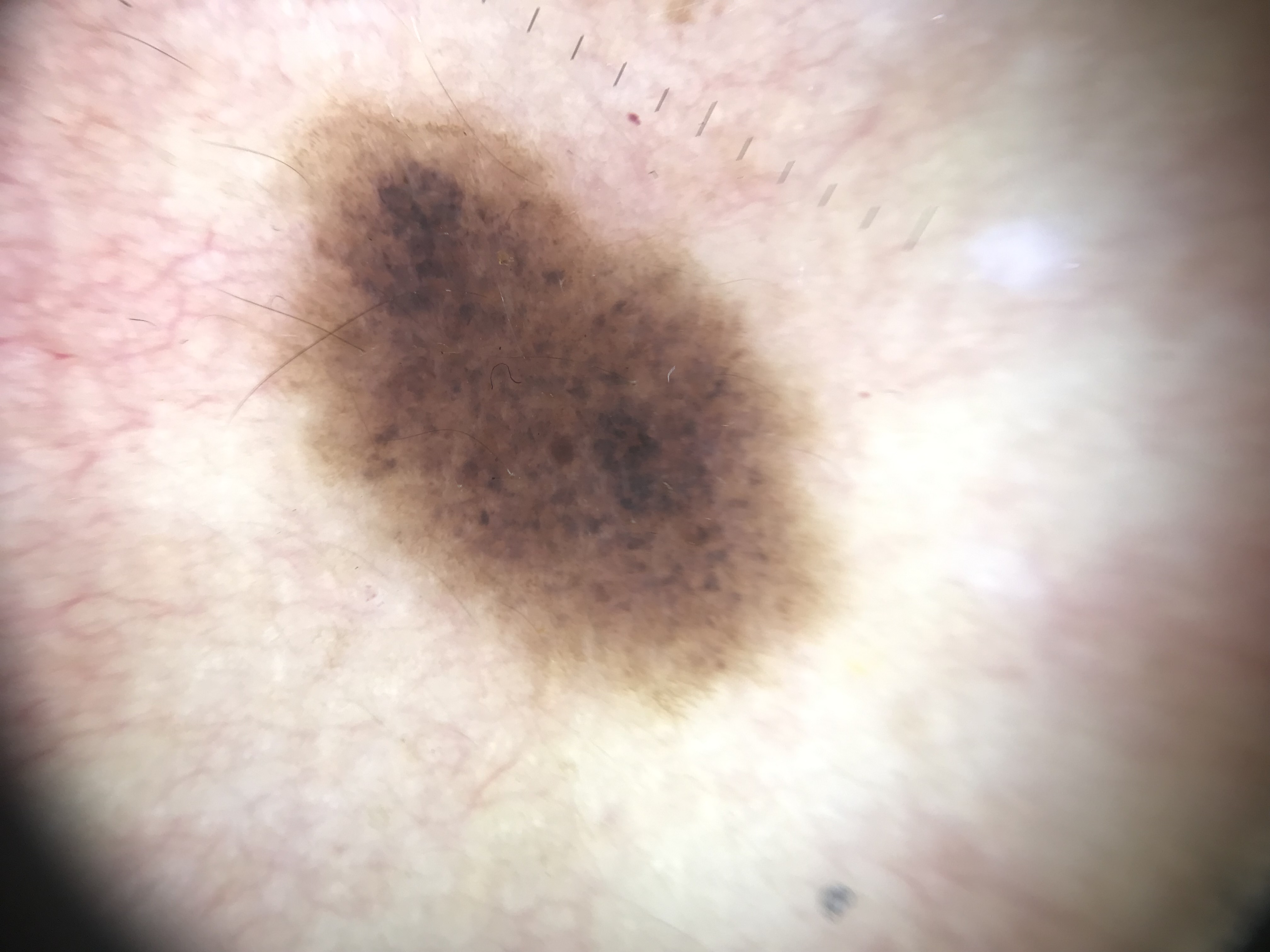A skin lesion imaged with a dermatoscope.
This is a banal lesion.
Classified as a congenital compound nevus.